A clinical close-up of a skin lesion · few moles overall by the patient's own estimate · a male patient age 78 · the patient says their skin reddens with sun exposure · on a questionnaire the patient reported a personal history of cancer · imaged for a research study, with no referral diagnosis recorded: 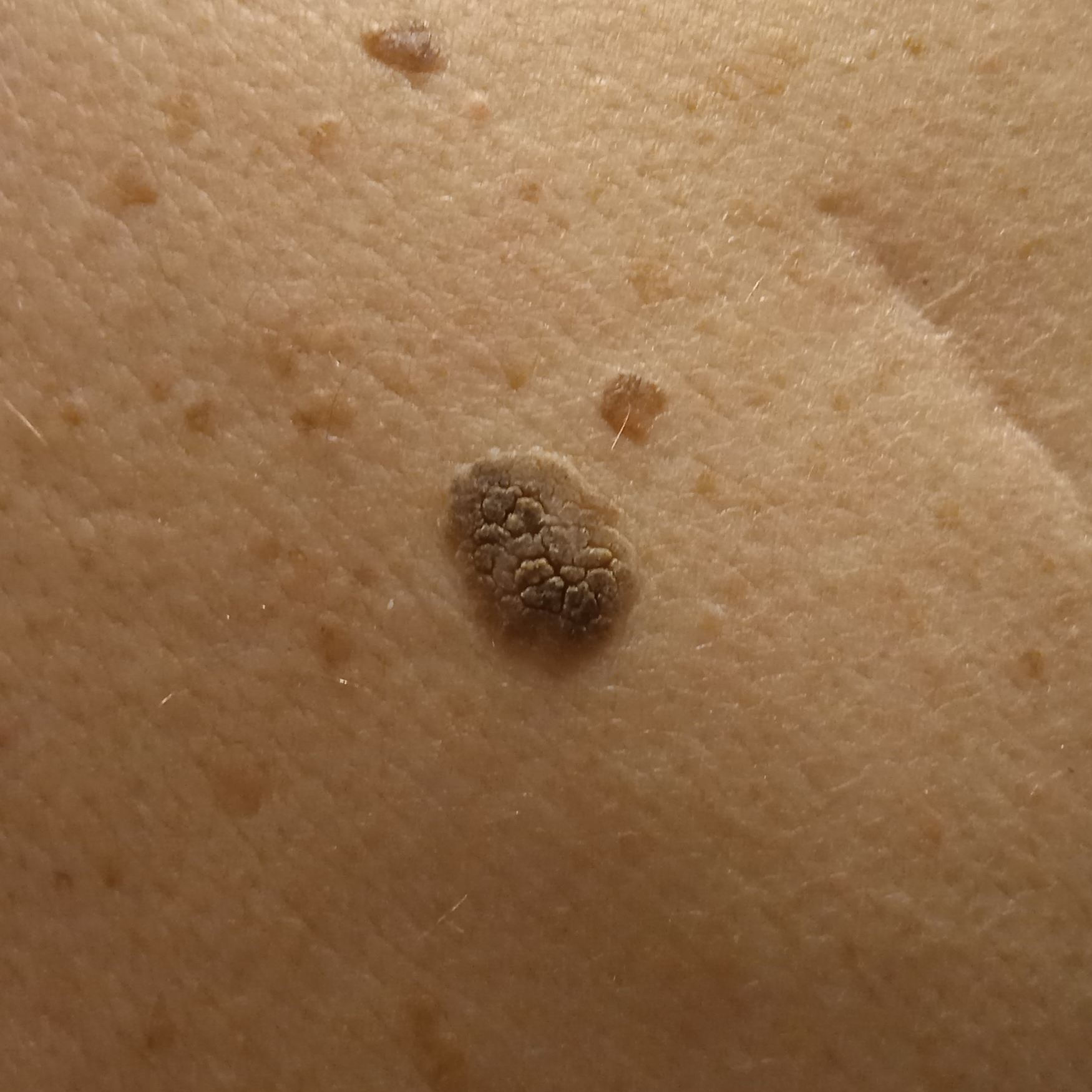location=the back; diameter=15.1 mm; assessment=seborrheic keratosis (dermatologist consensus).